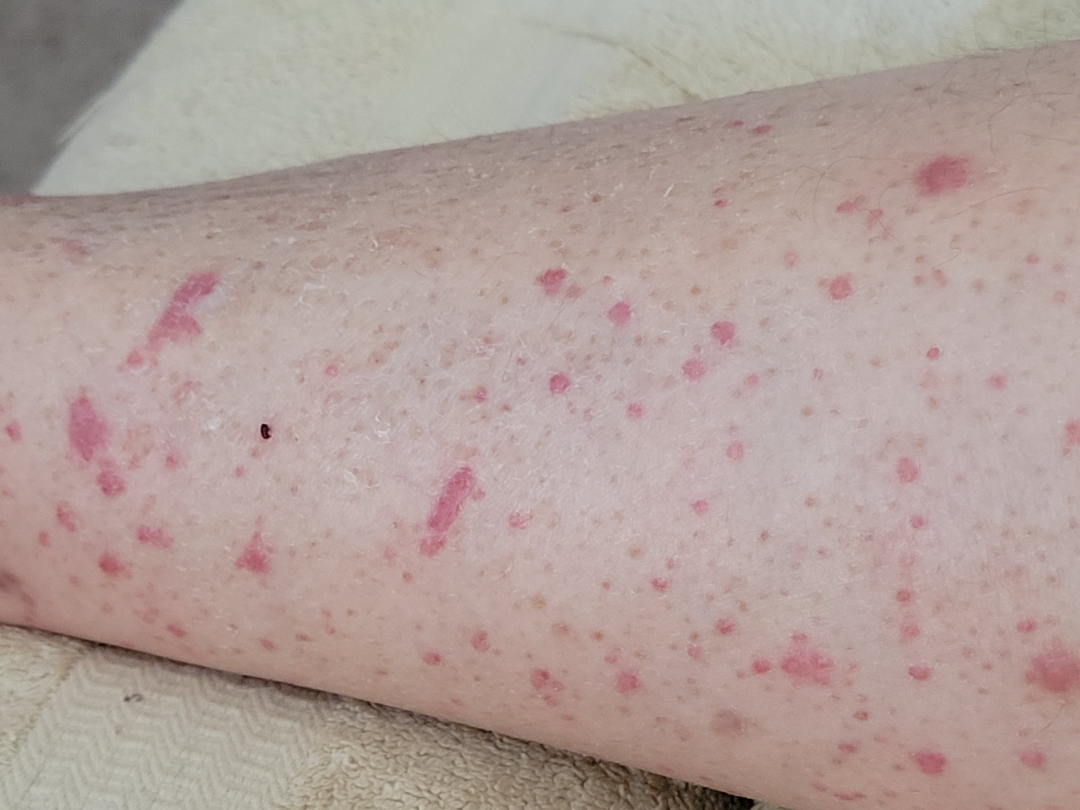Findings: No differential diagnosis could be assigned on photographic review. Background: Male subject, age 50–59. The affected area is the leg. Reported duration is less than one week. The patient did not report lesion symptoms. The contributor reports the lesion is raised or bumpy. Close-up view.